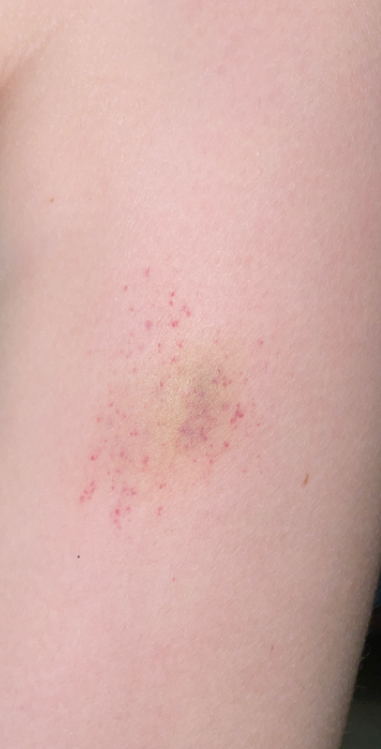The lesion involves the leg.
This image was taken at a distance.